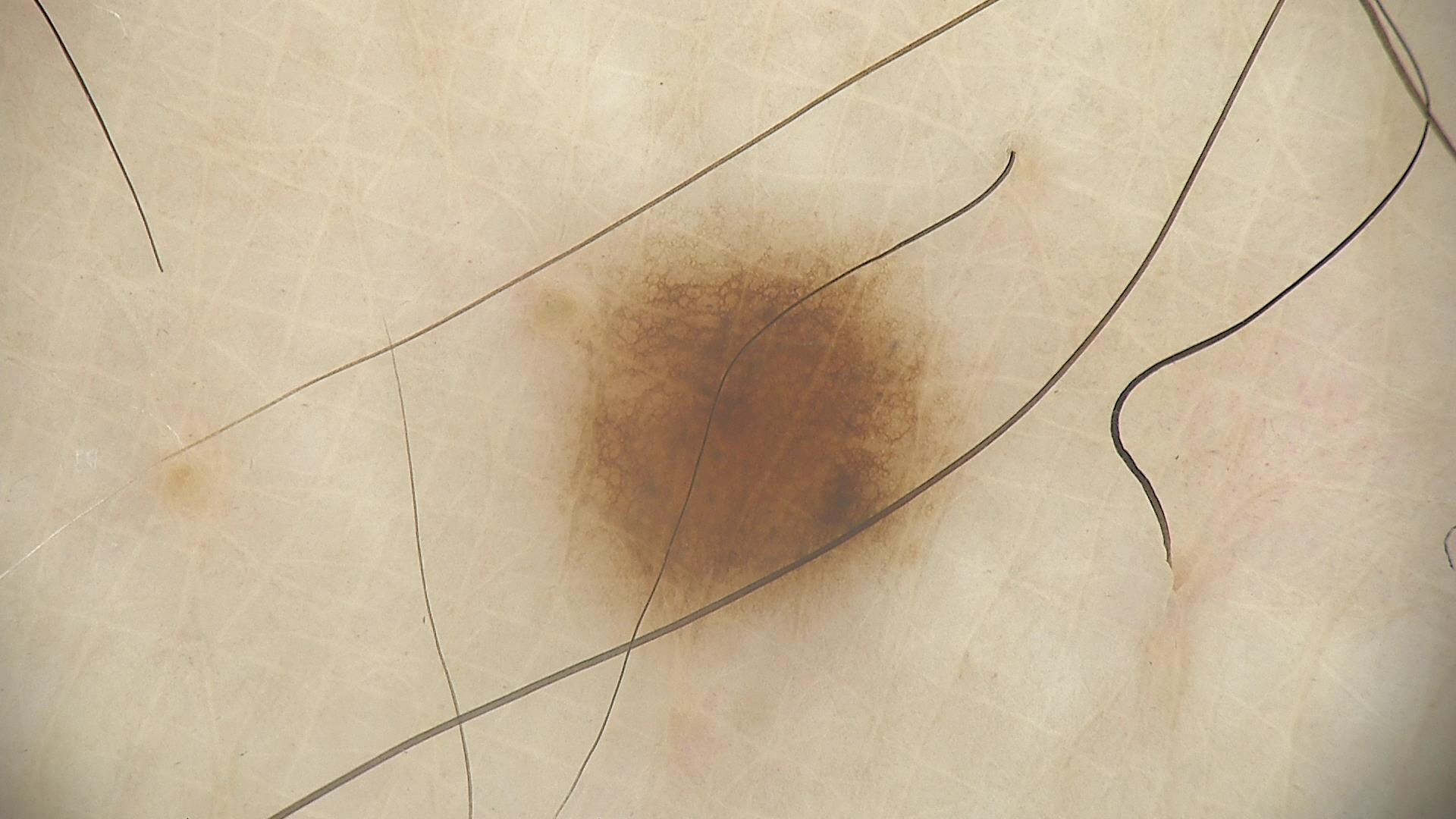{
  "image": "dermoscopy",
  "diagnosis": {
    "name": "dysplastic junctional nevus",
    "code": "jd",
    "malignancy": "benign",
    "super_class": "melanocytic",
    "confirmation": "expert consensus"
  }
}